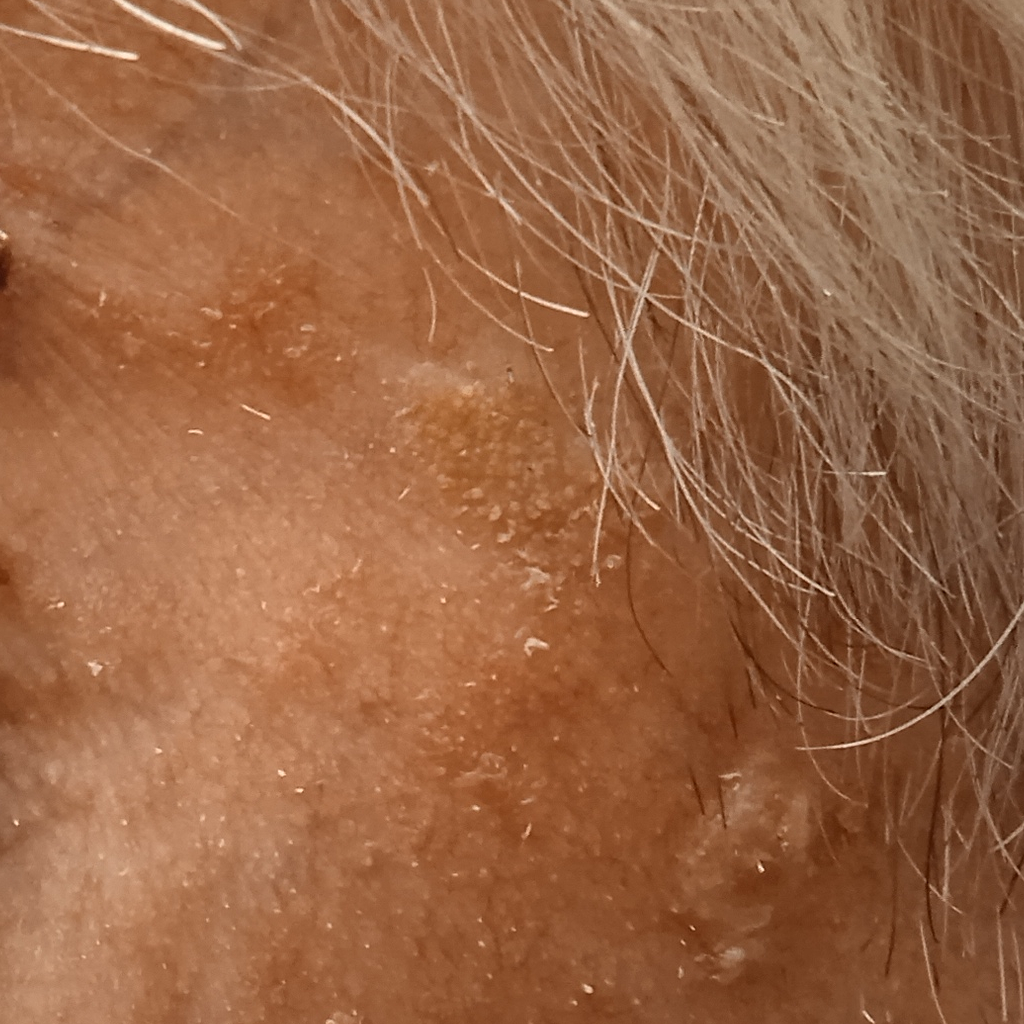Collected as part of a research study, without a referral diagnosis.
A male patient 89 years old.
Located on the face.
The lesion is about 8.8 mm across.
The dermatologists' assessment was a seborrheic keratosis.